A dermoscopic photograph of a skin lesion.
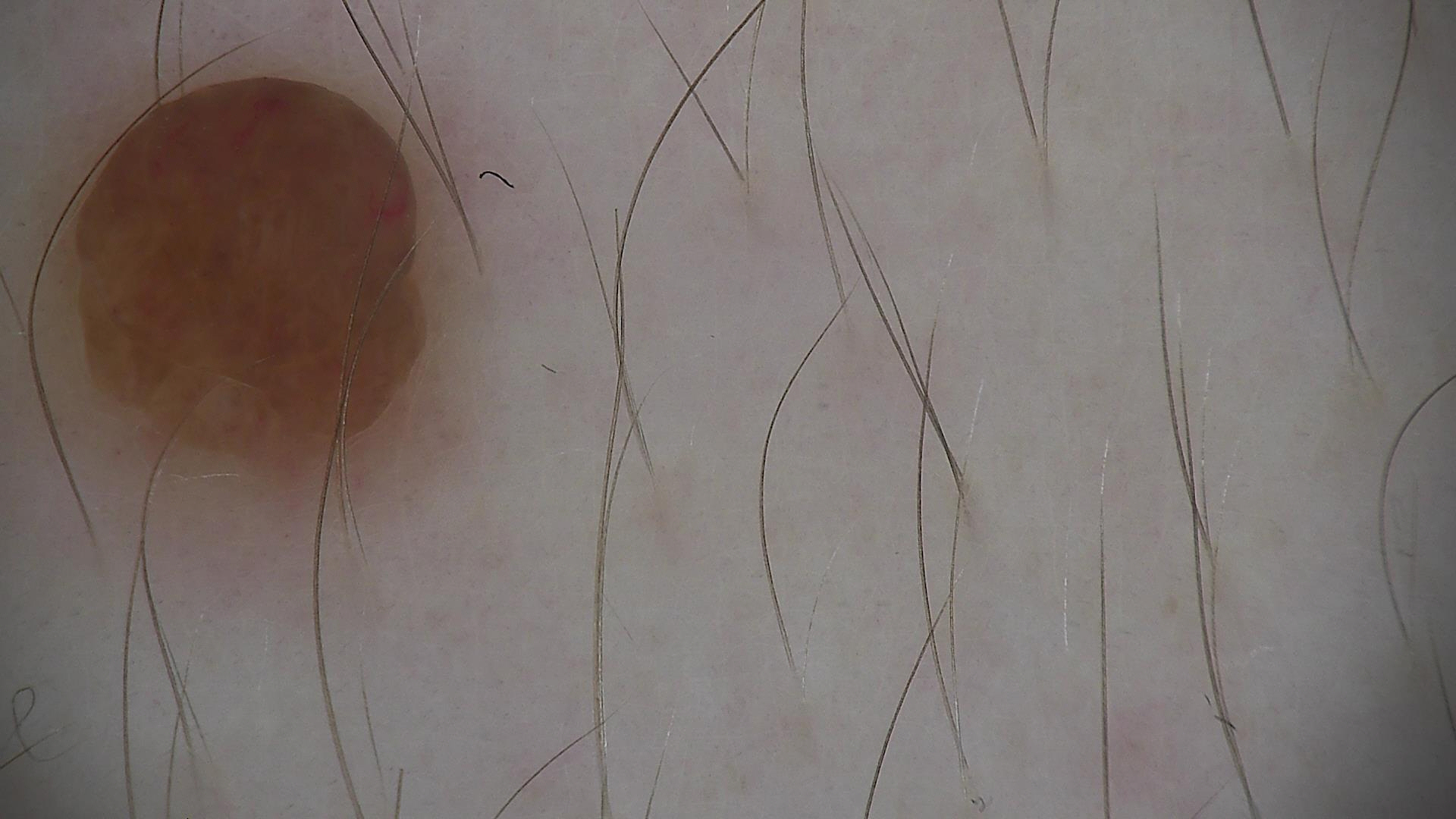Impression:
Labeled as a banal lesion — a dermal nevus.